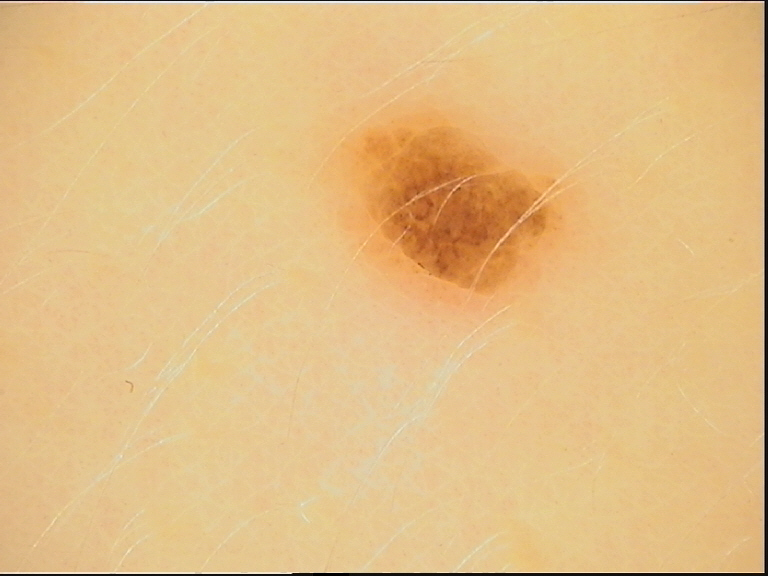image type: dermoscopy; diagnosis: compound nevus (expert consensus).